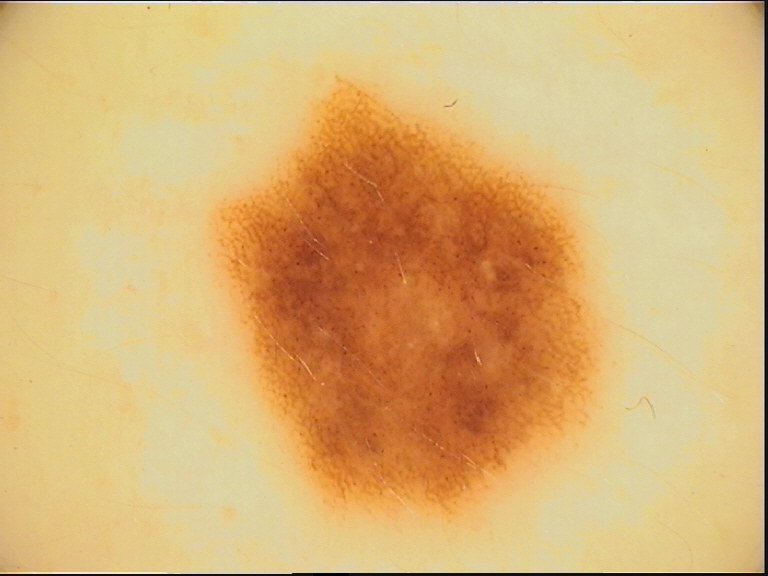* image type — dermatoscopy
* class — dysplastic junctional nevus (expert consensus)